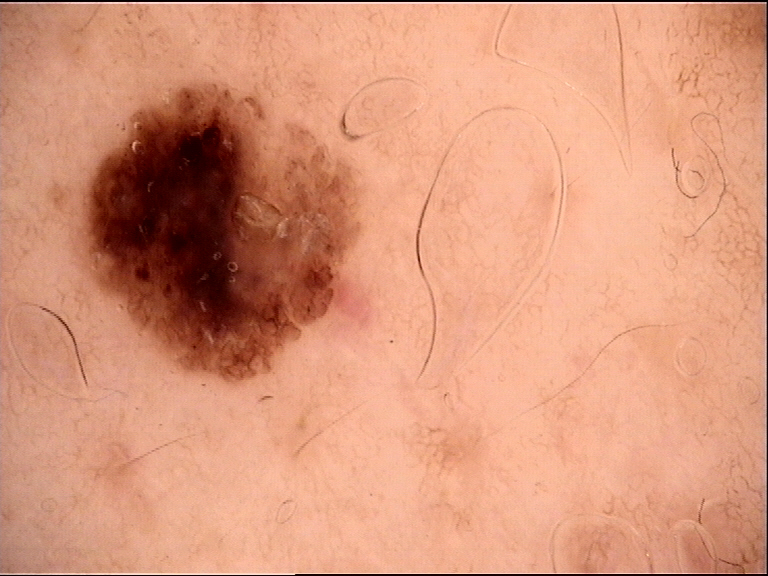- modality — dermoscopy
- class — dysplastic compound nevus (expert consensus)